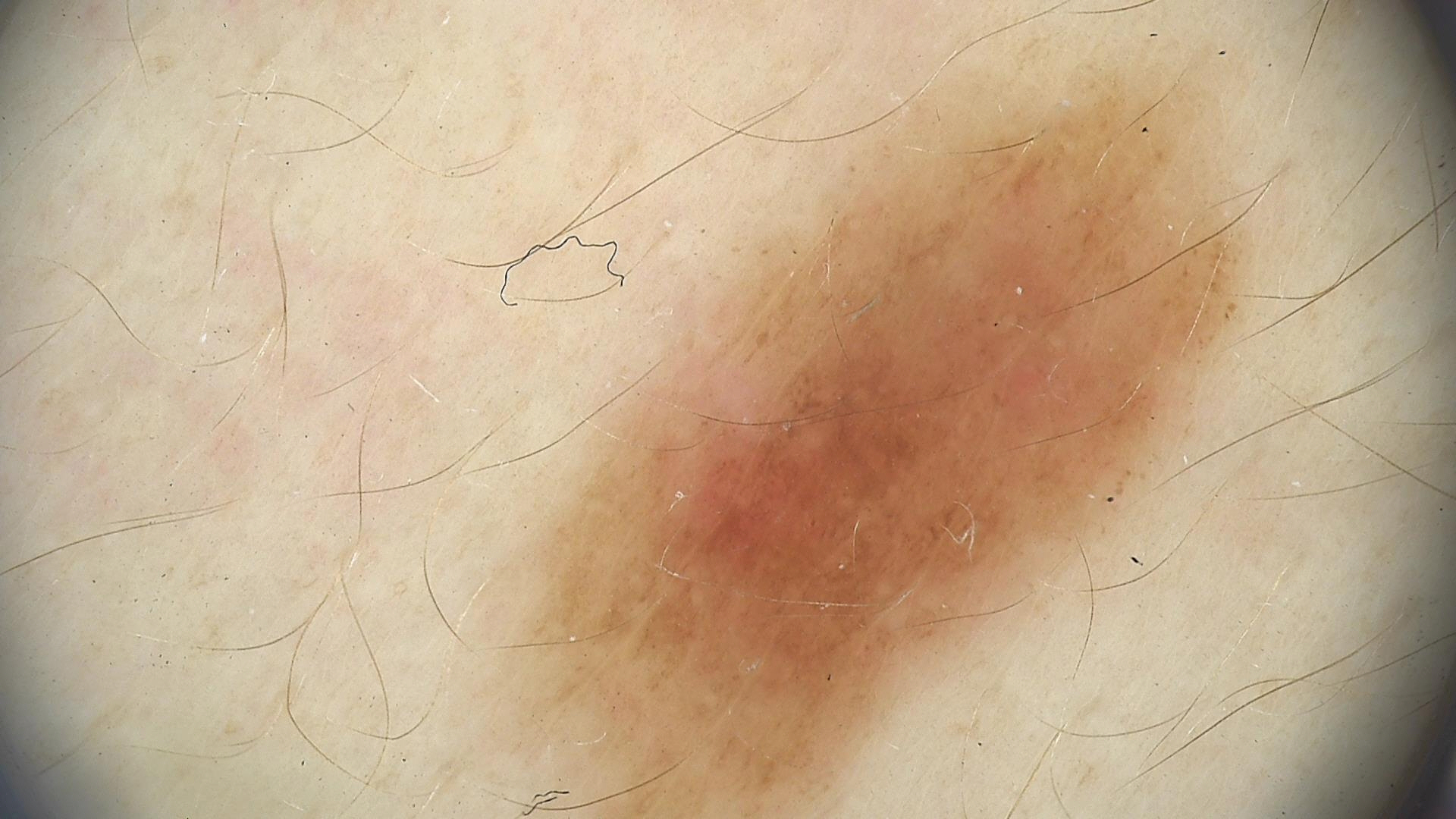Diagnosed as a dysplastic junctional nevus.